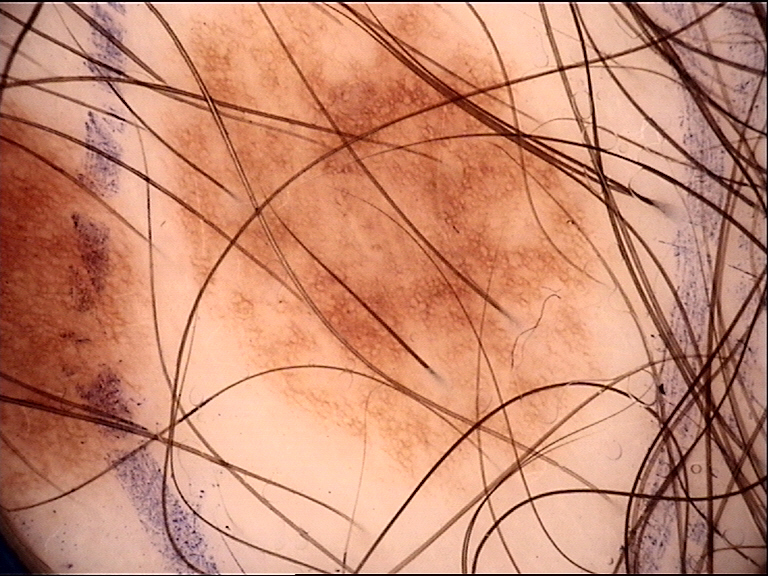image type=dermatoscopy
diagnosis=dysplastic junctional nevus (expert consensus)